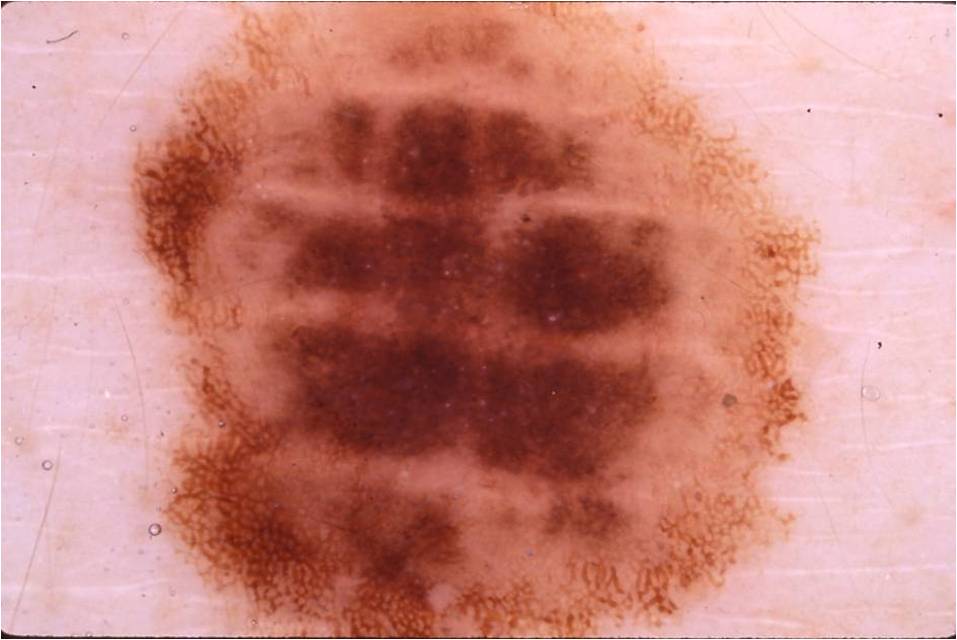Case summary:
Dermoscopy of a skin lesion. The subject is a female aged 18 to 22. The dermoscopic pattern shows pigment network. With coordinates (x1, y1, x2, y2), lesion location: [130,2,824,638].
Impression:
Consistent with a melanocytic nevus, a benign lesion.